The photograph was taken at an angle; the lesion involves the arm; female patient, age 30–39:
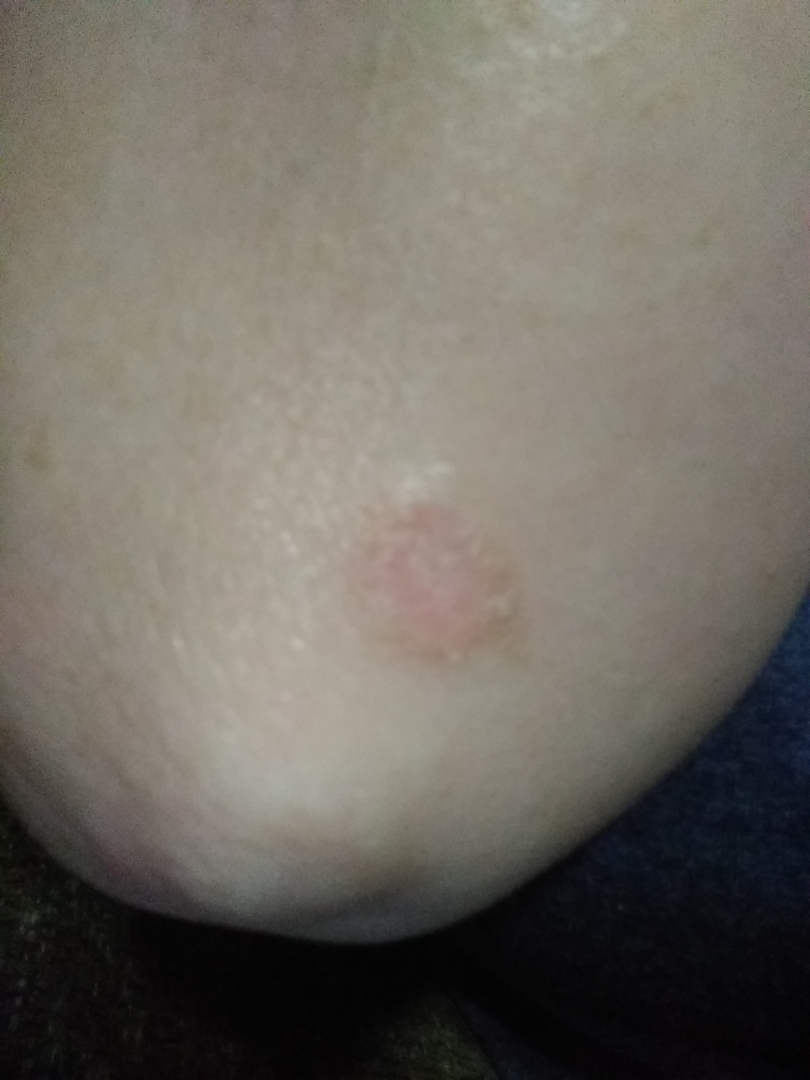assessment = a single dermatologist reviewed the case: Tinea, Psoriasis and Eczema were considered with similar weight.